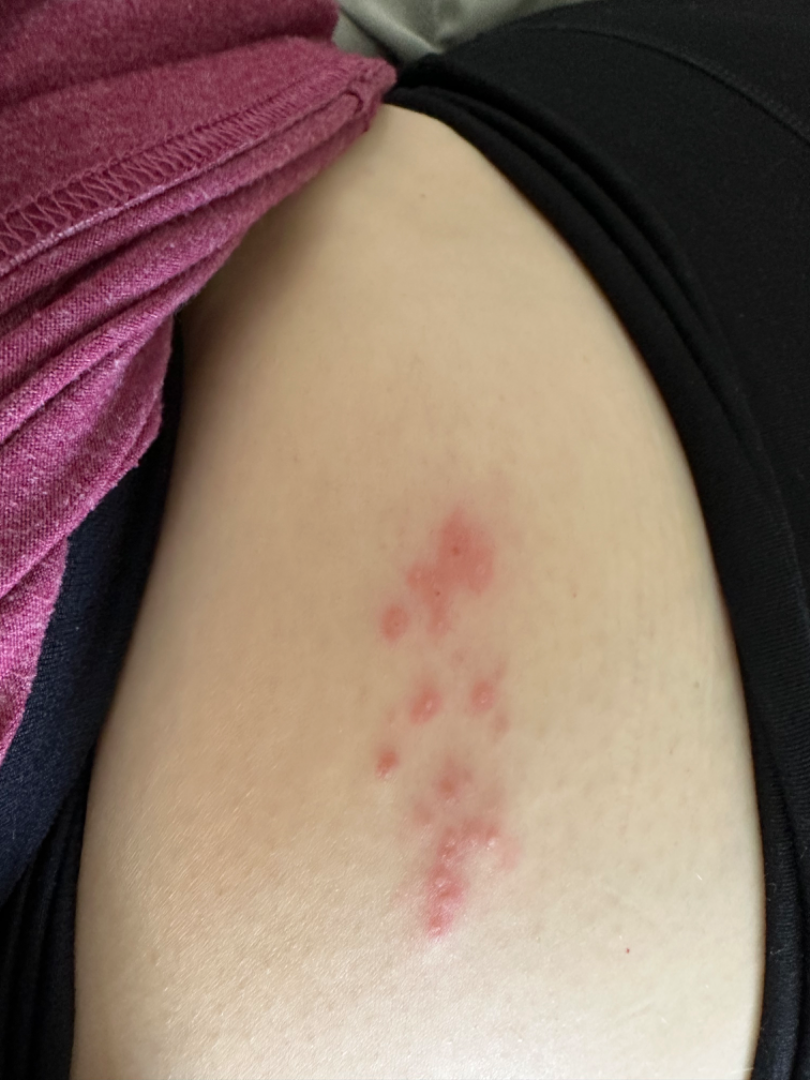Reported duration is less than one week. The front of the torso is involved. The photograph is a close-up of the affected area. The patient described the issue as a rash. The lesion is described as raised or bumpy. Symptoms reported: pain, darkening and itching. Herpes Simplex (55%); Herpes Zoster (27%); Skin and soft tissue atypical mycobacterial infection (18%).